A skin lesion imaged with a dermatoscope:
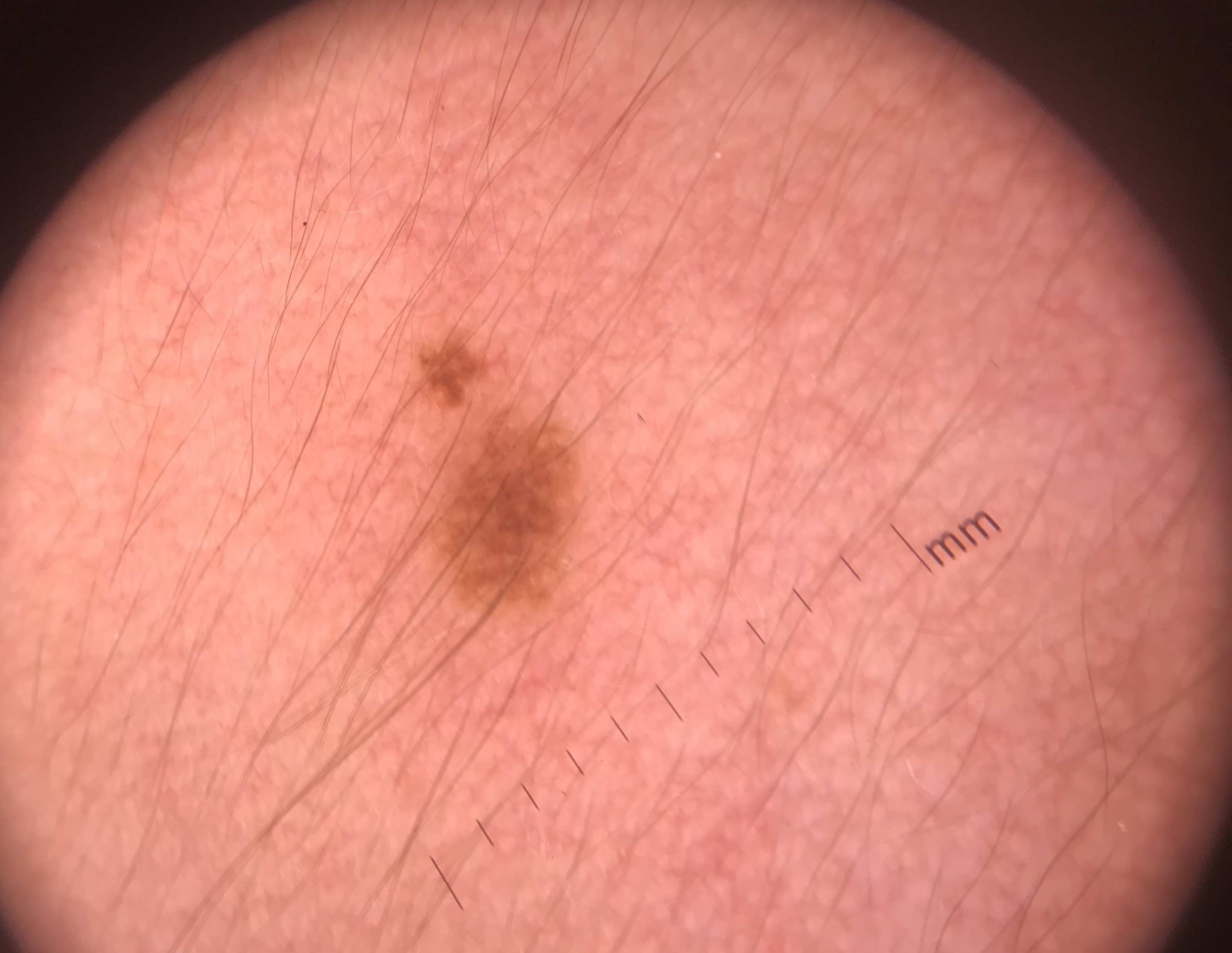Findings:
* classification: banal
* assessment: junctional nevus (expert consensus)